A female patient aged 33 to 37 · a skin lesion imaged with contact-polarized dermoscopy · FST II · the chart records no melanoma in first-degree relatives and no previous melanoma.
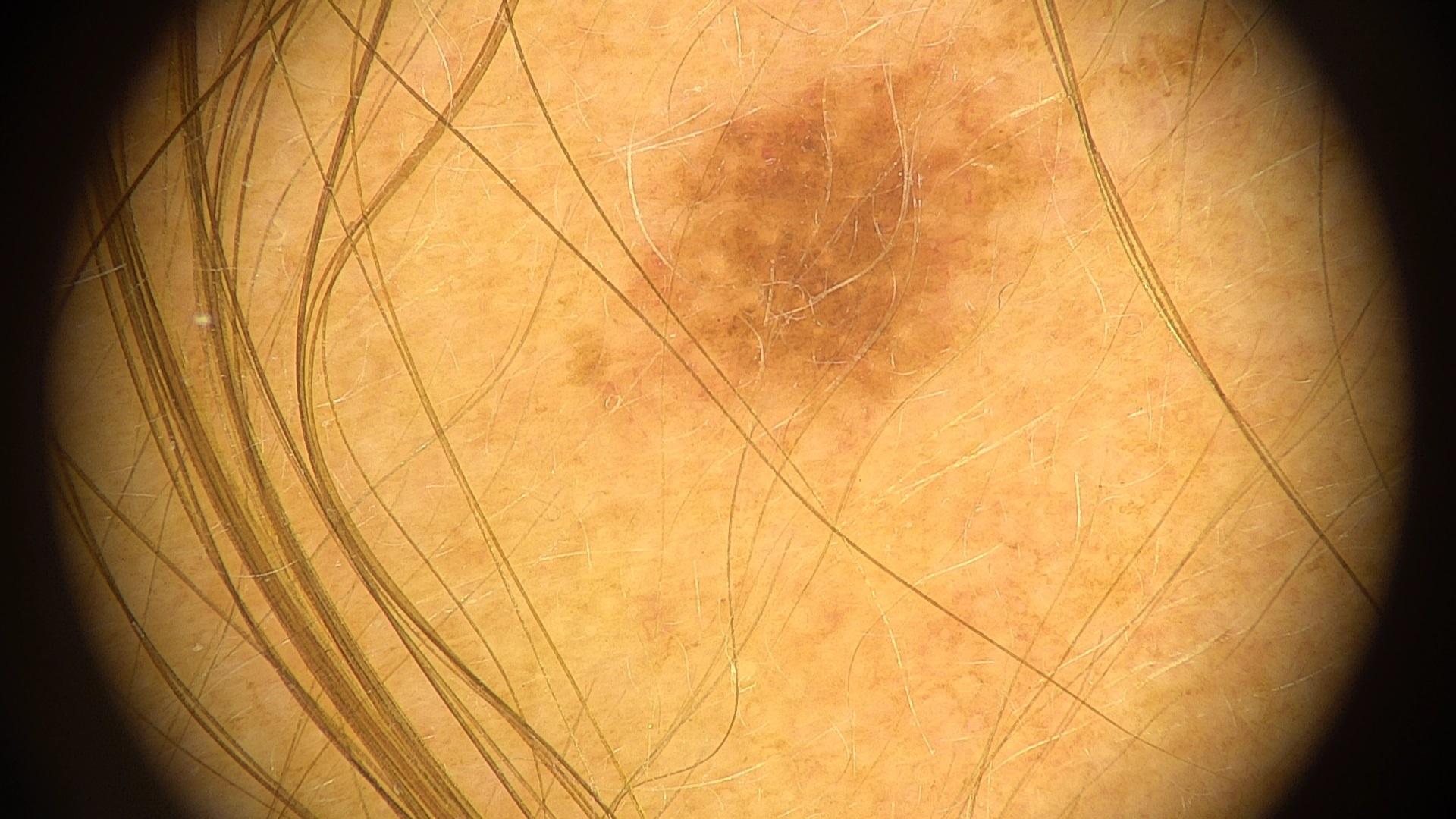Summary:
The lesion is on a lower extremity.
Impression:
The clinical assessment was a melanocytic lesion — a nevus.